A dermoscopic image of a skin lesion:
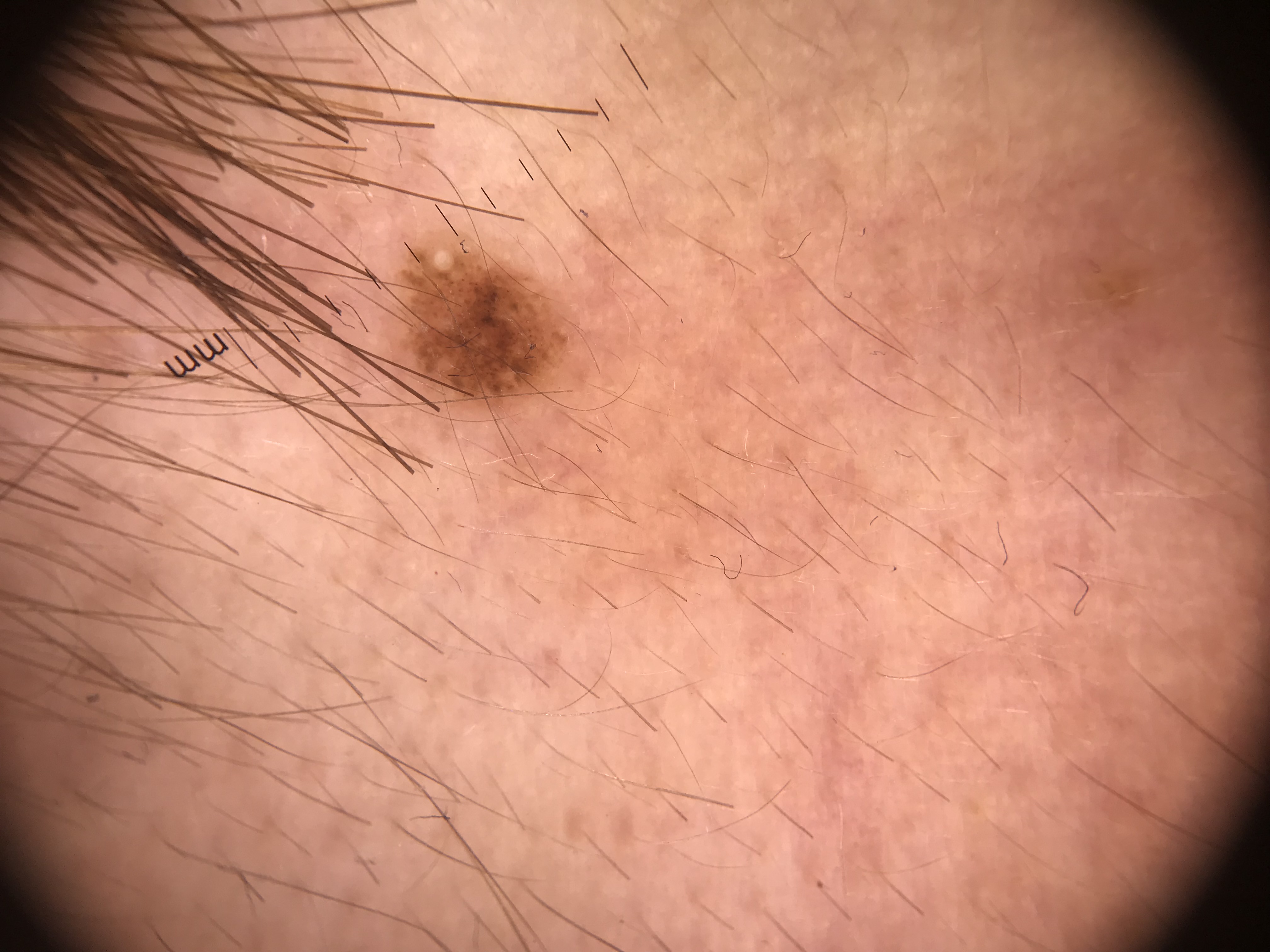Conclusion:
Classified as a Miescher nevus.